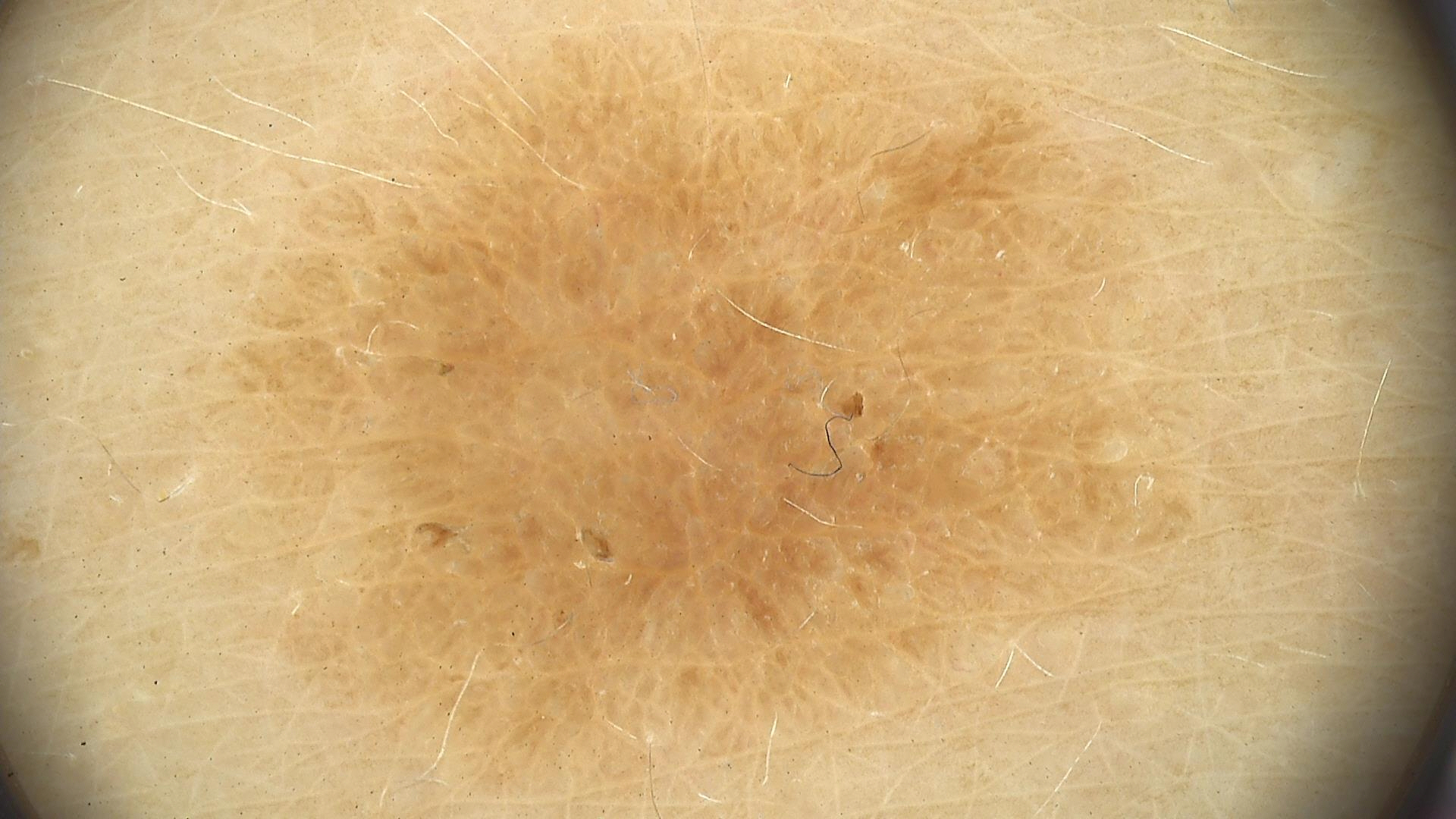class = seborrheic keratosis (expert consensus).